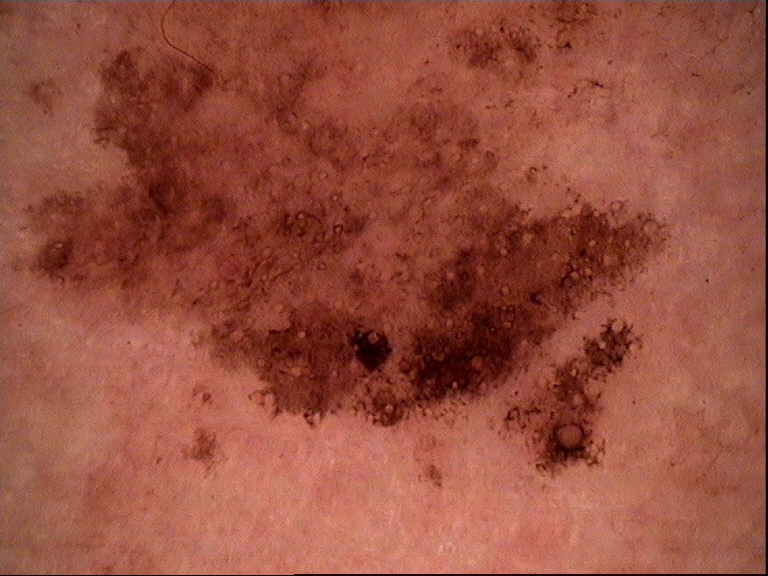A dermoscopic close-up of a skin lesion. Diagnosed as a benign lesion — a solar lentigo.